This image was taken at an angle · skin tone: FST III.
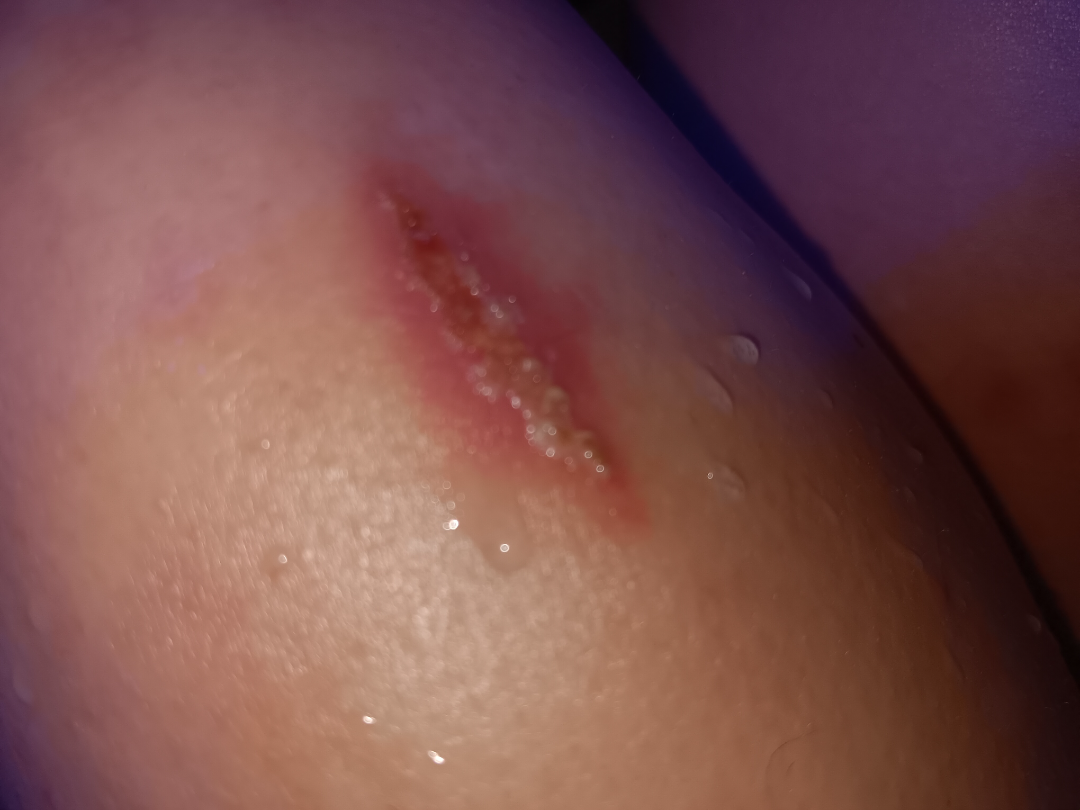Q: What is the differential diagnosis?
A: Allergic Contact Dermatitis (1.00)